Dermoscopy of a skin lesion.
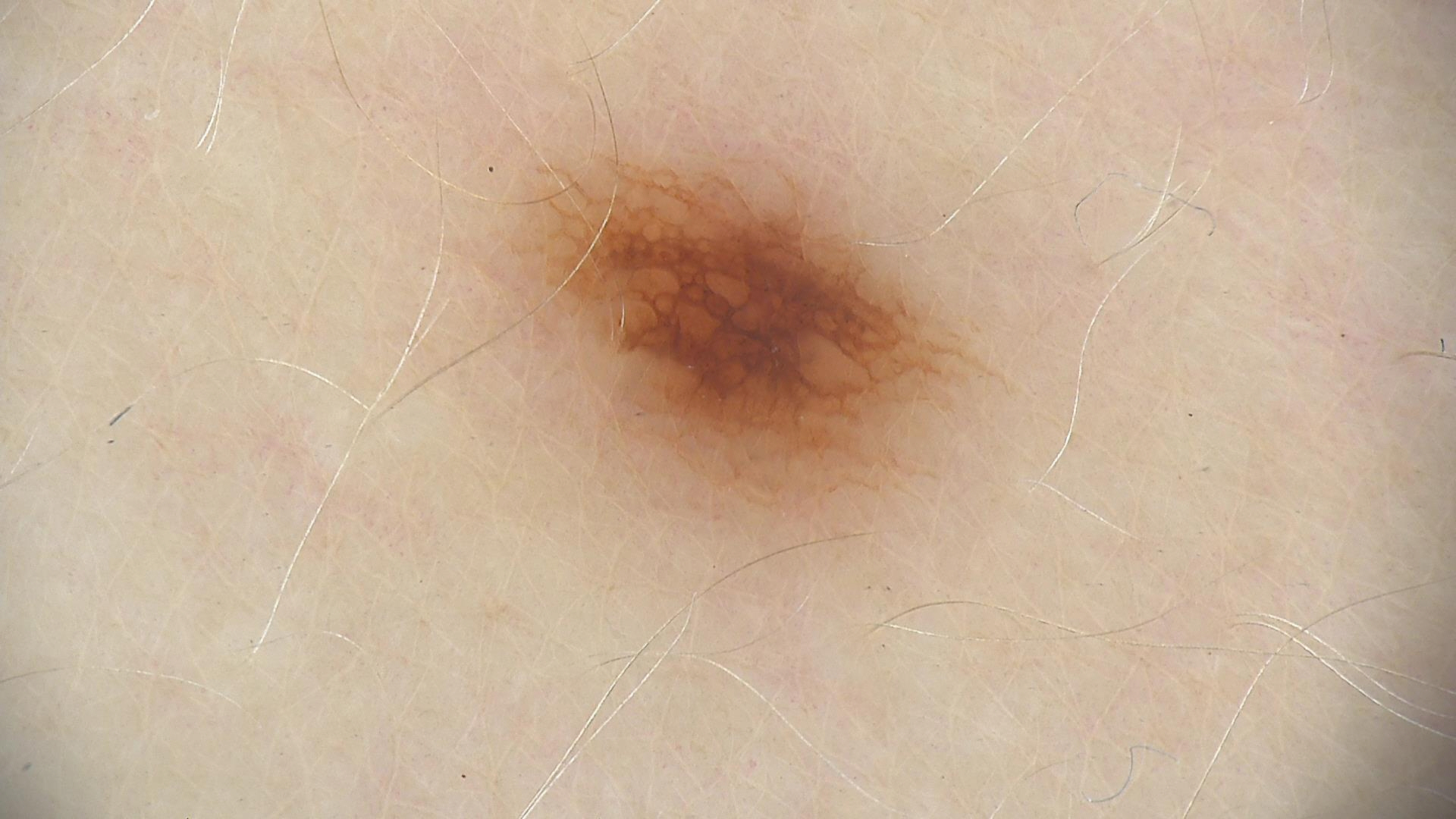Conclusion:
Consistent with a dysplastic junctional nevus.